An image taken at an angle · the patient reports the lesion is raised or bumpy · skin tone: Fitzpatrick III.
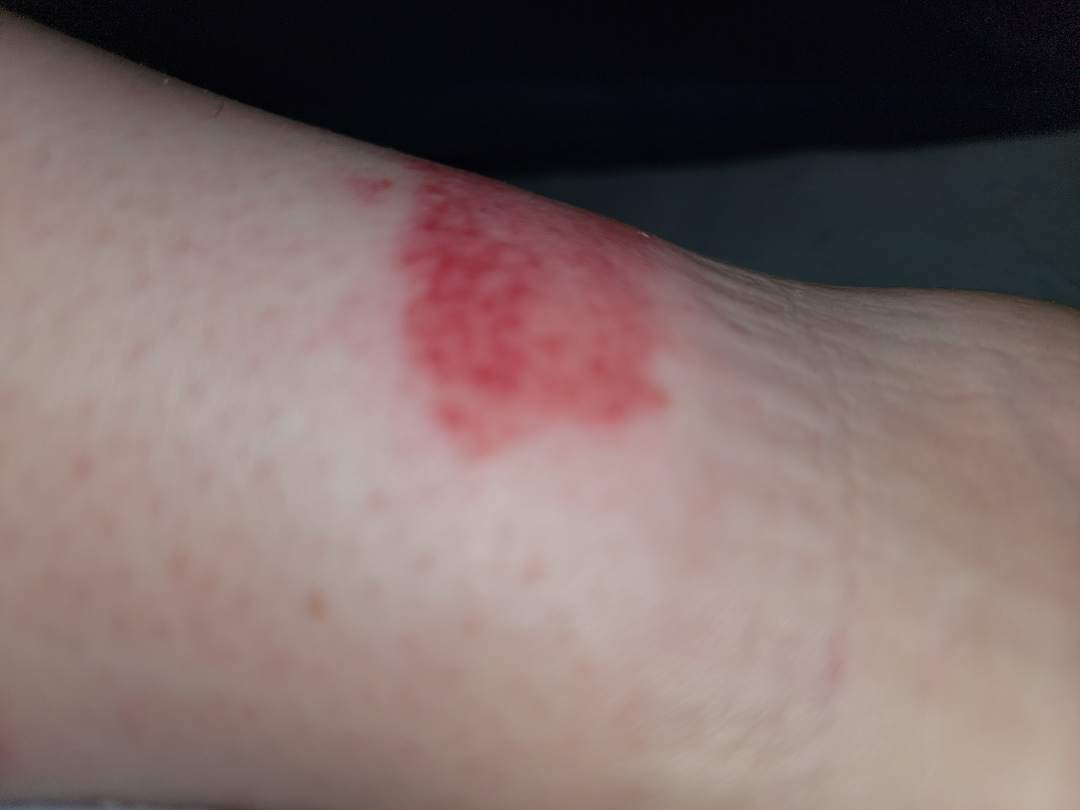{"differential": {"tied_lead": ["Eczema", "Allergic Contact Dermatitis", "Irritant Contact Dermatitis"]}}